An image taken at a distance · the affected area is the back of the hand · the contributor is a female aged 50–59: 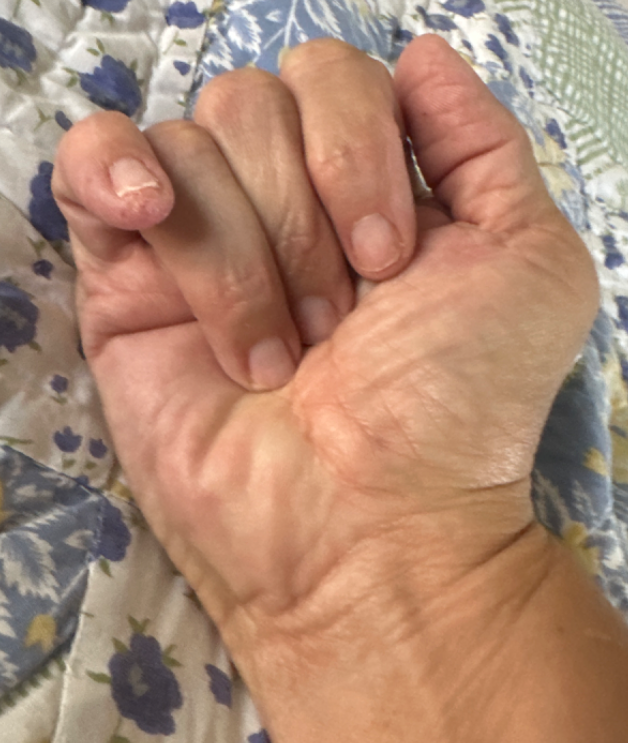Impression:
The reviewing clinician's impression was: in keeping with Acute-on-chronic dyshidrotic eczema of hands.